Texture is reported as fluid-filled and raised or bumpy, this is a close-up image, the subject is male, the head or neck is involved, the contributor reports associated fatigue and joint pain, symptoms reported: bothersome appearance and itching, the patient considered this a nail problem:
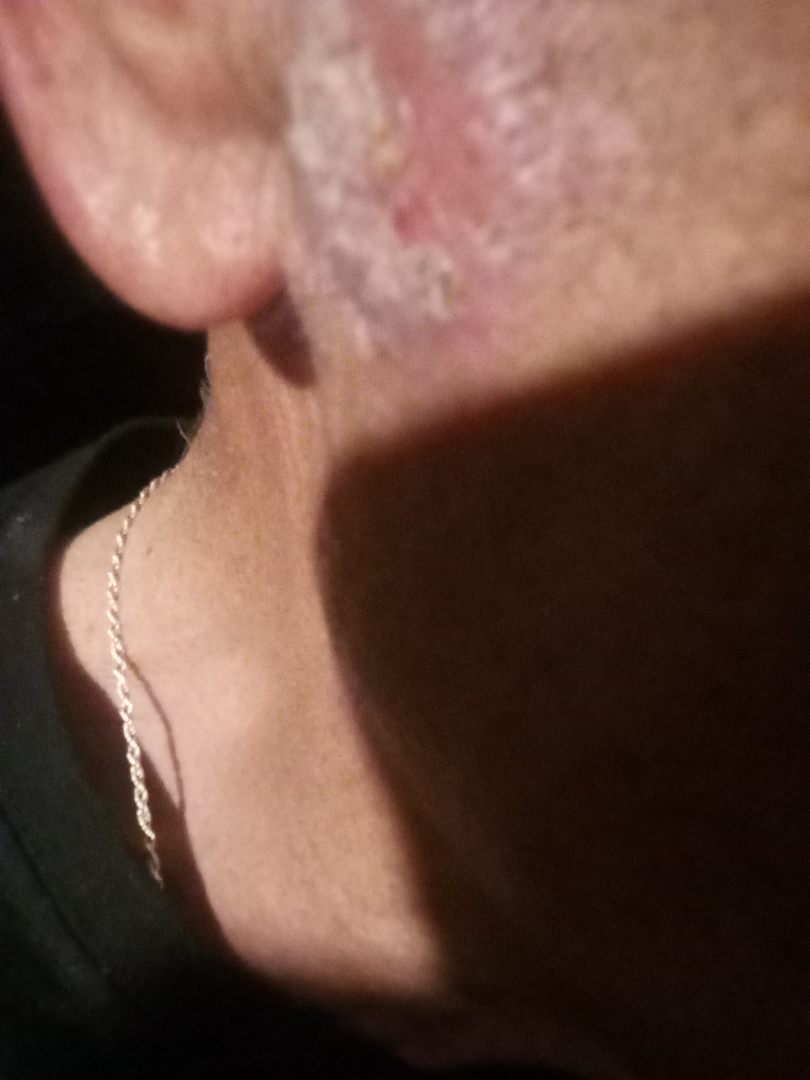Review:
The dermatologist could not determine a likely condition from the photograph alone.